A dermoscopic close-up of a skin lesion.
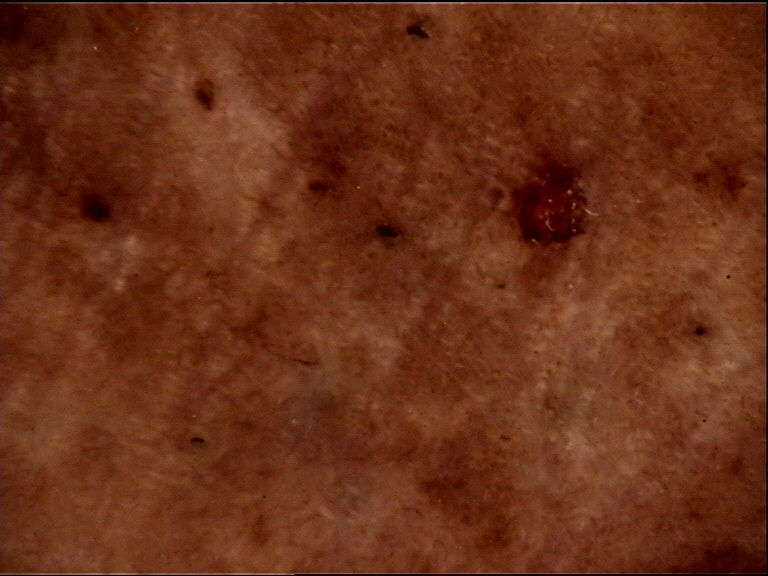diagnostic label: congenital compound nevus (expert consensus)